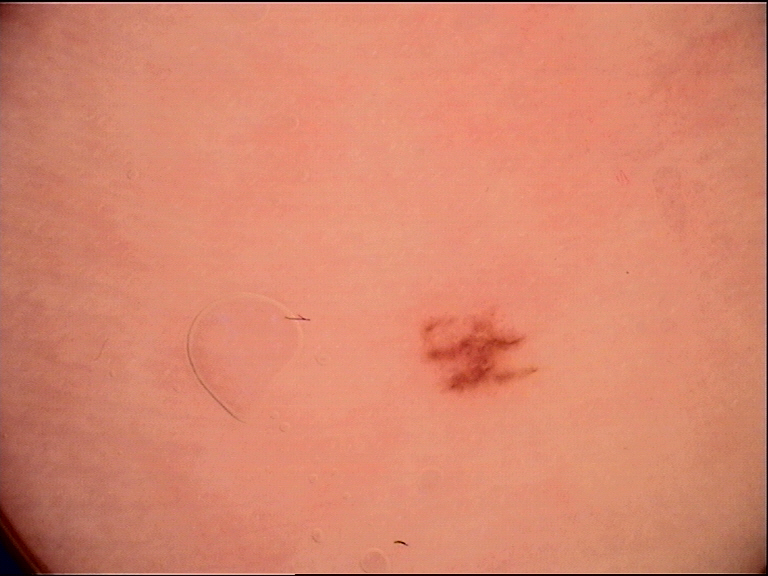label — acral junctional nevus (expert consensus).